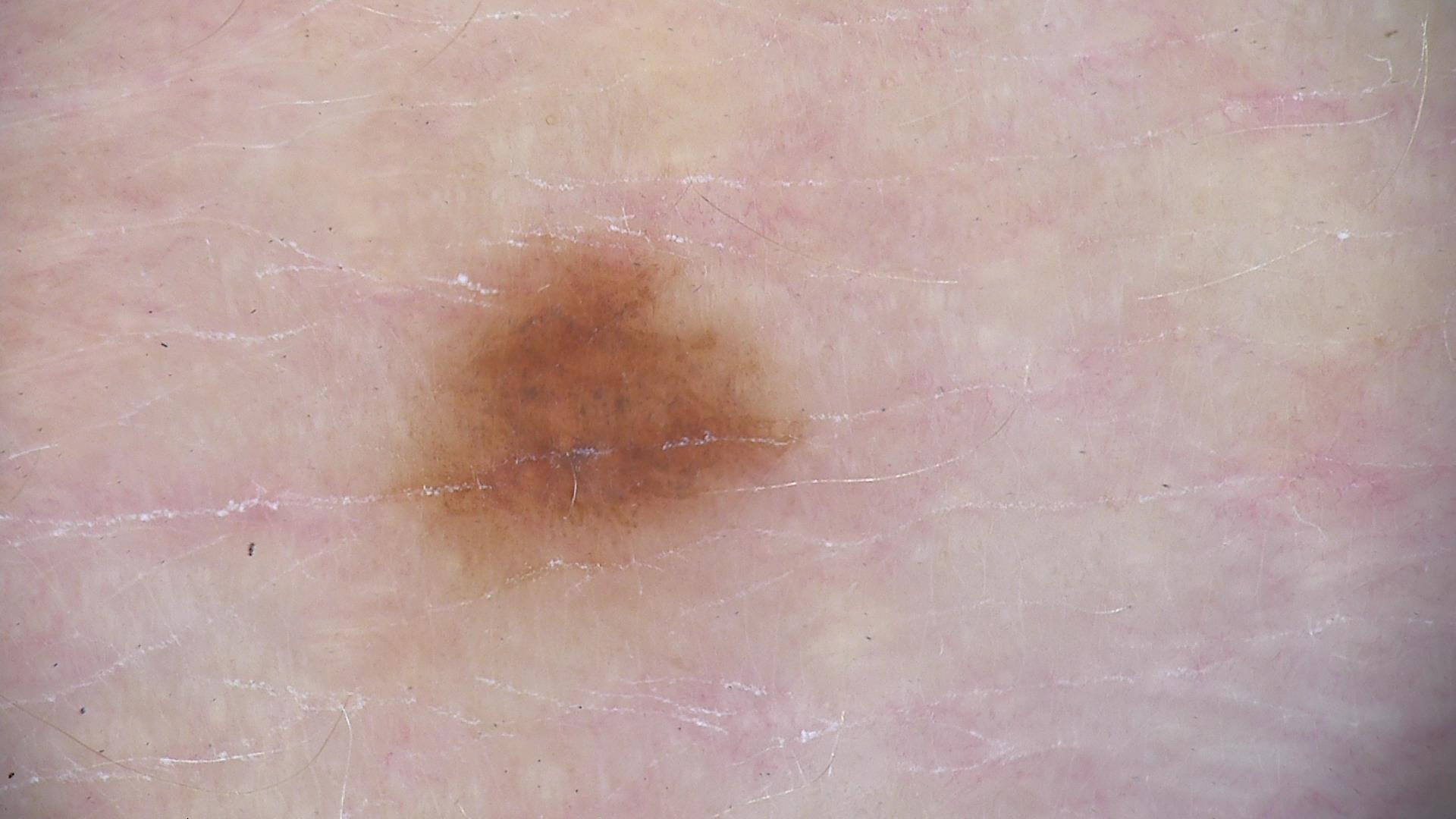Impression: Classified as a dysplastic junctional nevus.